A dermatoscopic image of a skin lesion:
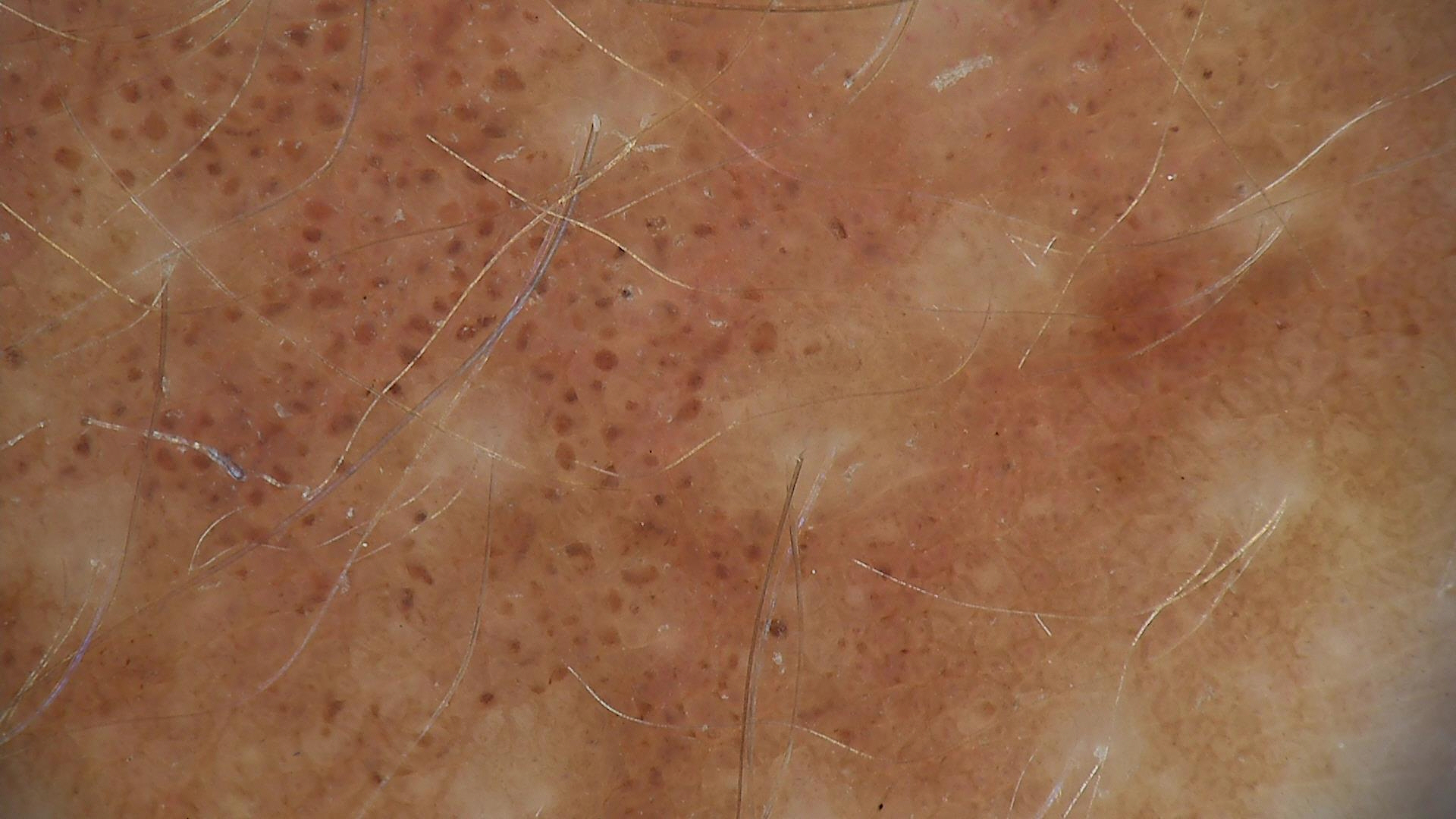Q: What is the diagnosis?
A: congenital junctional nevus (expert consensus)